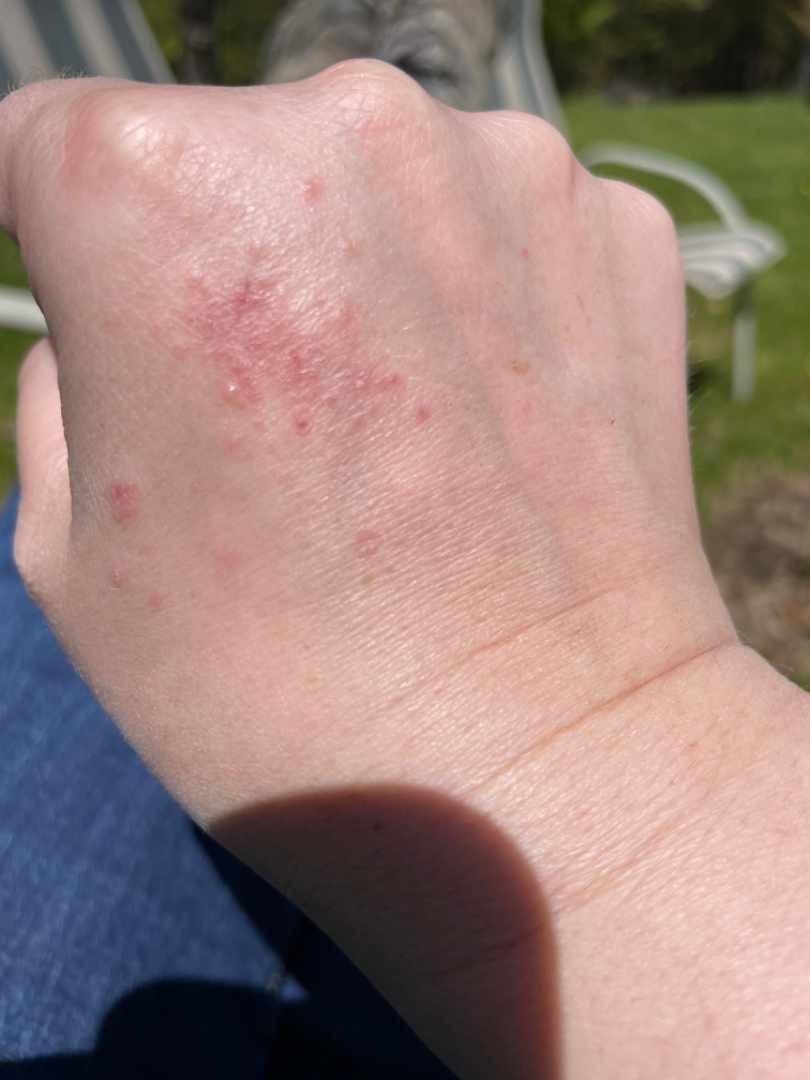body_site: back of the hand
shot_type: close-up
differential:
  leading:
    - Irritant Contact Dermatitis
  considered:
    - Allergic Contact Dermatitis